Dermoscopy of a skin lesion.
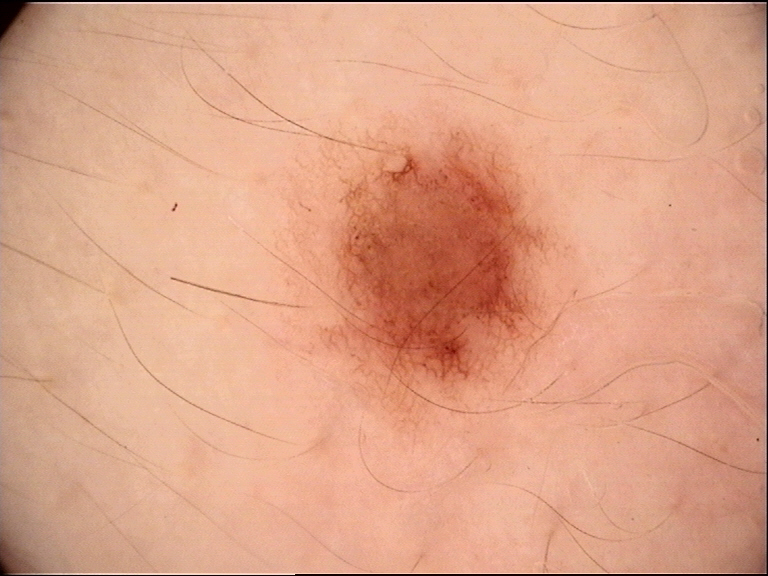<case>
<diagnosis>
<name>dysplastic junctional nevus</name>
<code>jd</code>
<malignancy>benign</malignancy>
<super_class>melanocytic</super_class>
<confirmation>expert consensus</confirmation>
</diagnosis>
</case>